A dermoscopic photograph of a skin lesion.
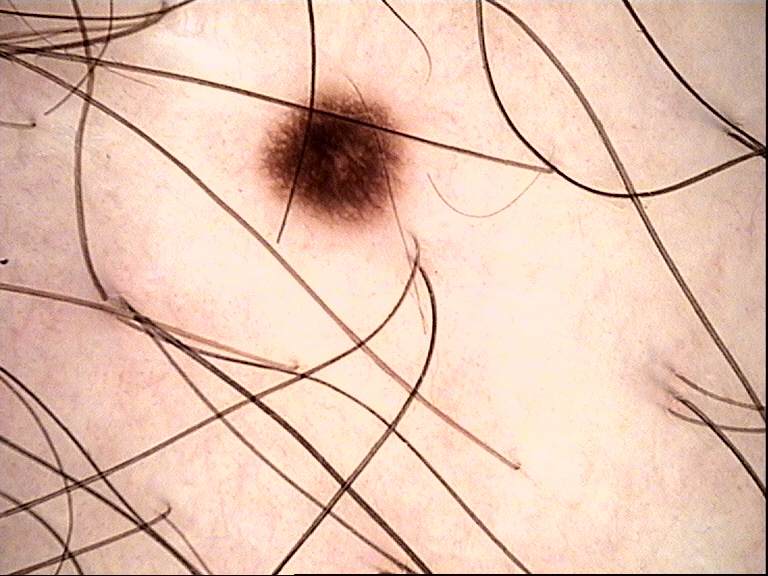Diagnosed as a benign lesion — a dysplastic junctional nevus.